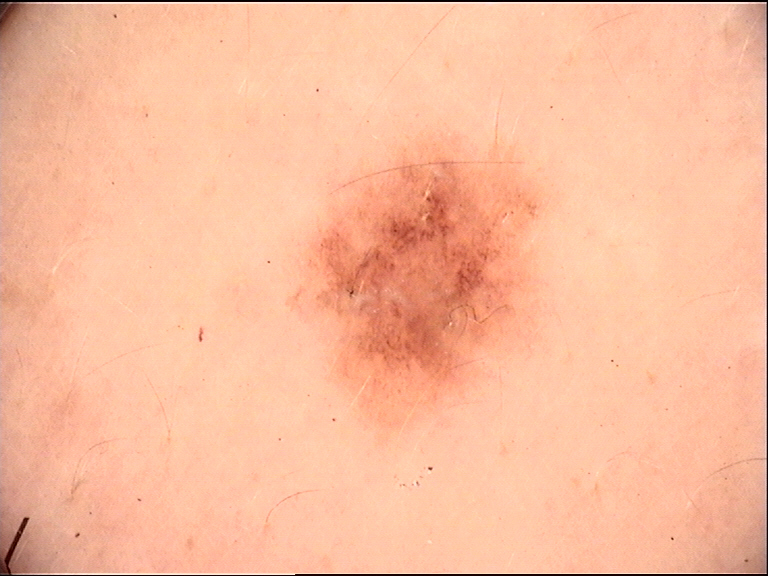diagnosis:
  name: dysplastic junctional nevus
  code: jd
  malignancy: benign
  super_class: melanocytic
  confirmation: expert consensus